A dermoscopic photograph of a skin lesion.
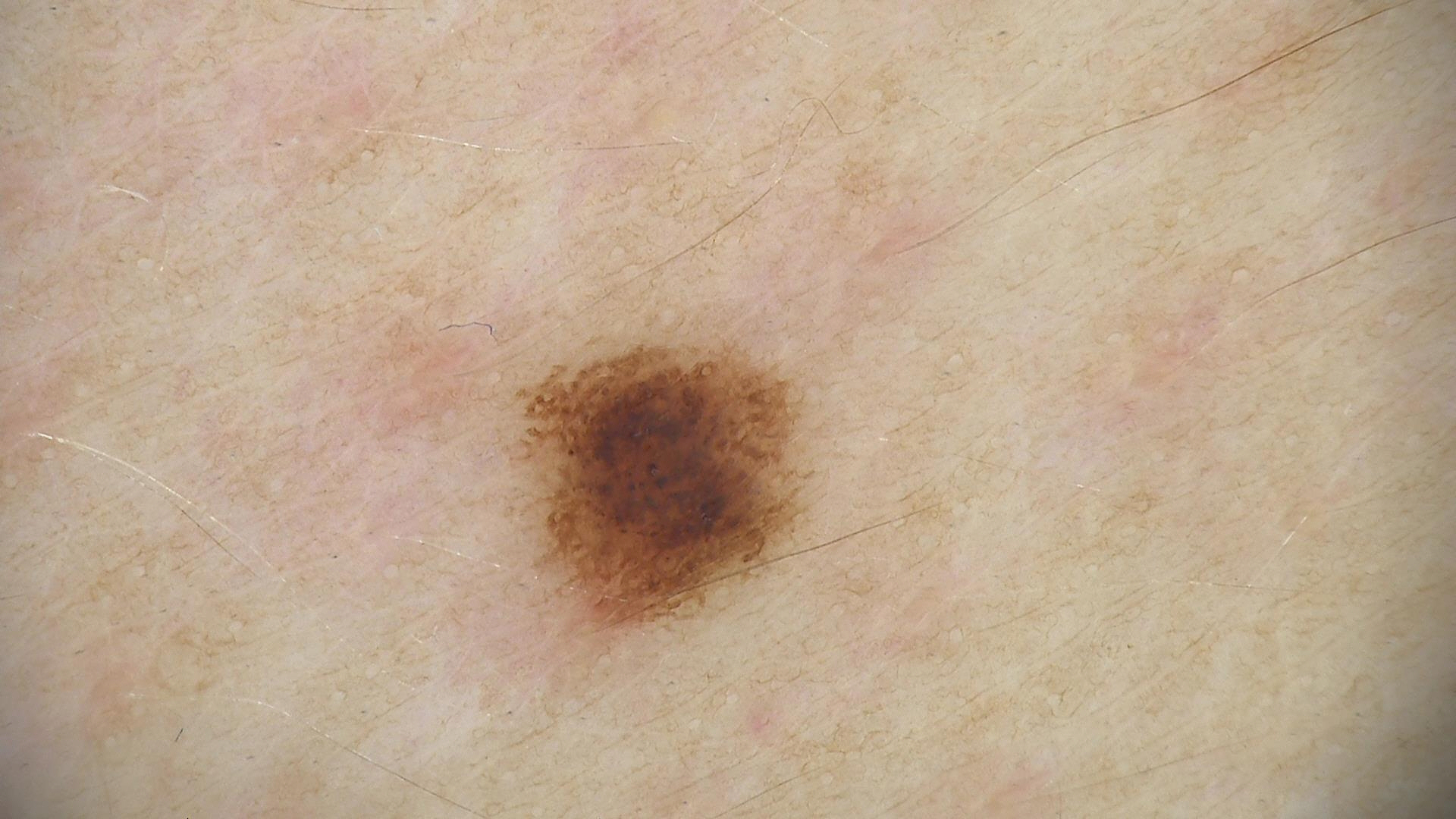The diagnostic label was a benign lesion — a dysplastic junctional nevus.